A dermoscopy image of a single skin lesion.
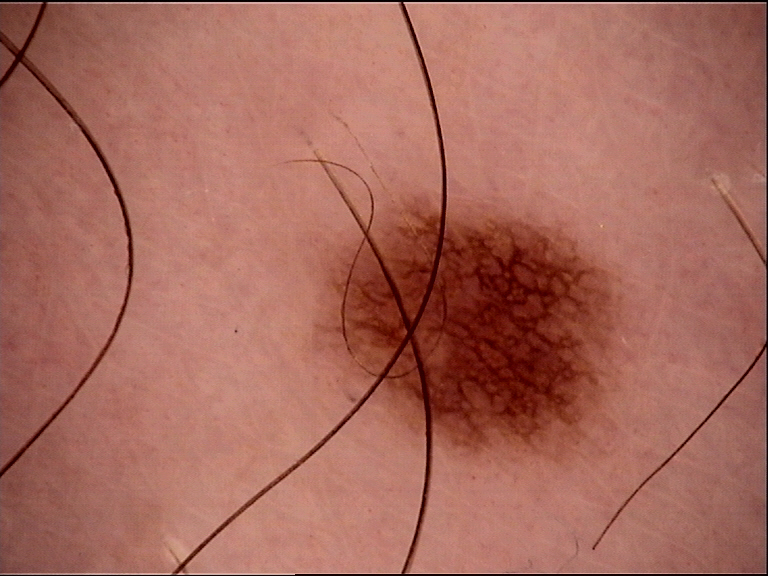Conclusion: The diagnostic label was a banal lesion — a junctional nevus.